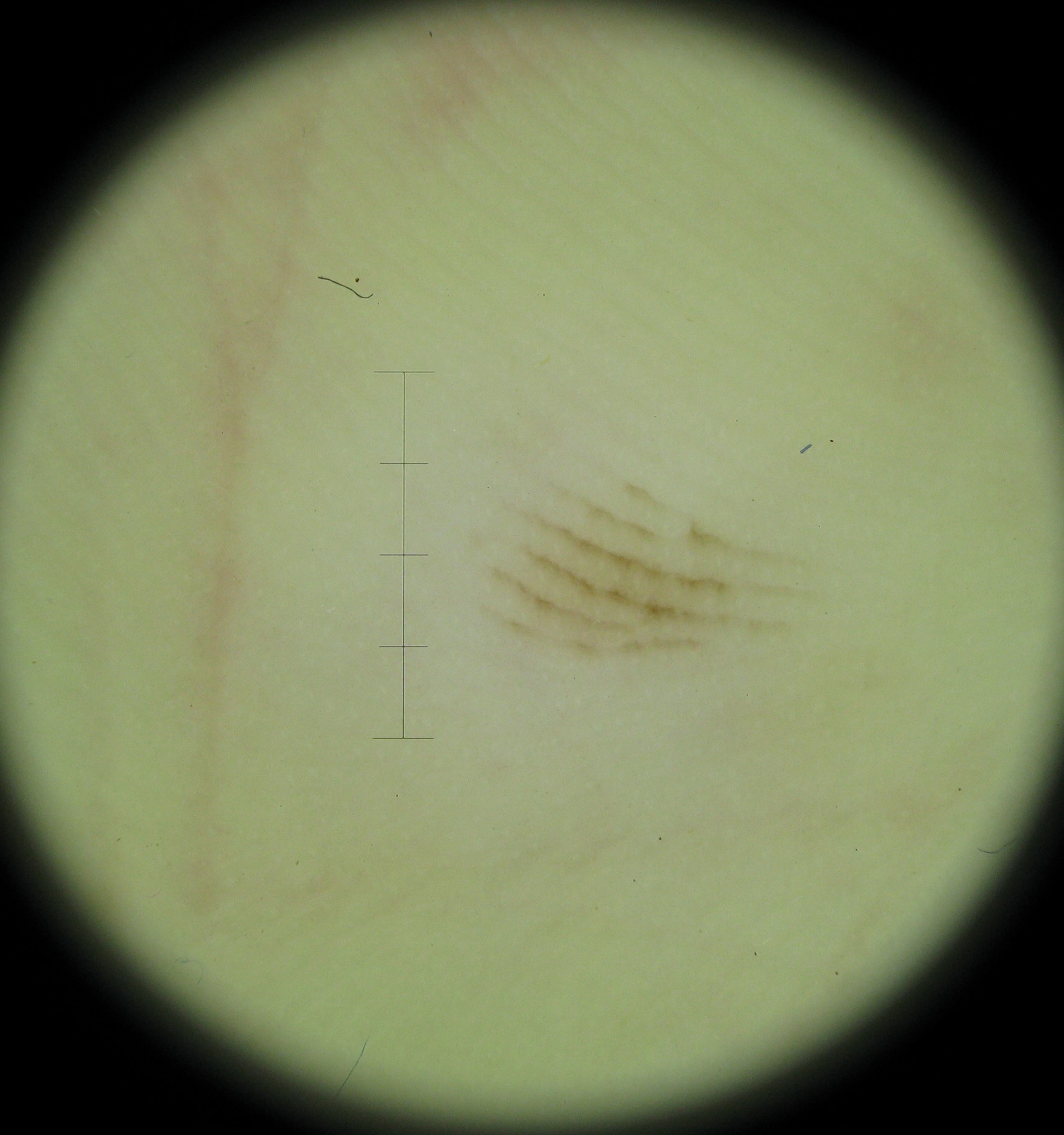Labeled as an acral junctional nevus.